A skin lesion imaged with a dermatoscope: 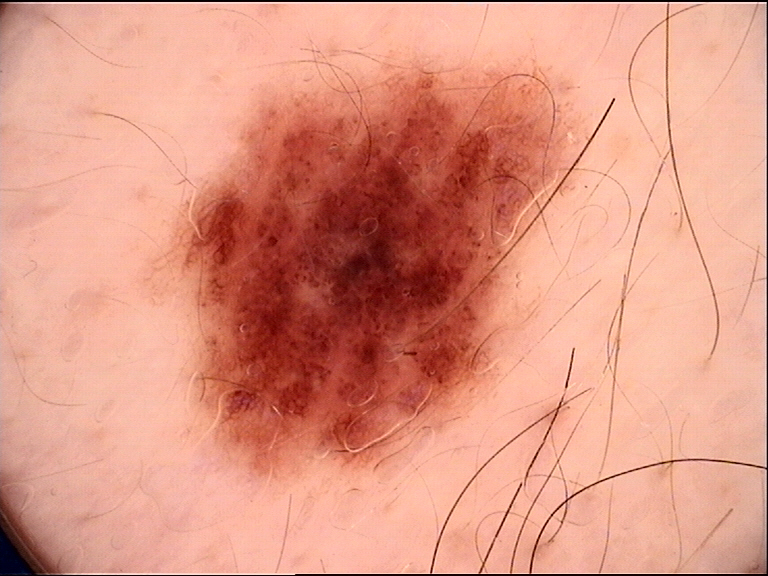Conclusion:
Consistent with a dysplastic compound nevus.